A male subject, approximately 70 years of age; a dermoscopic close-up of a skin lesion.
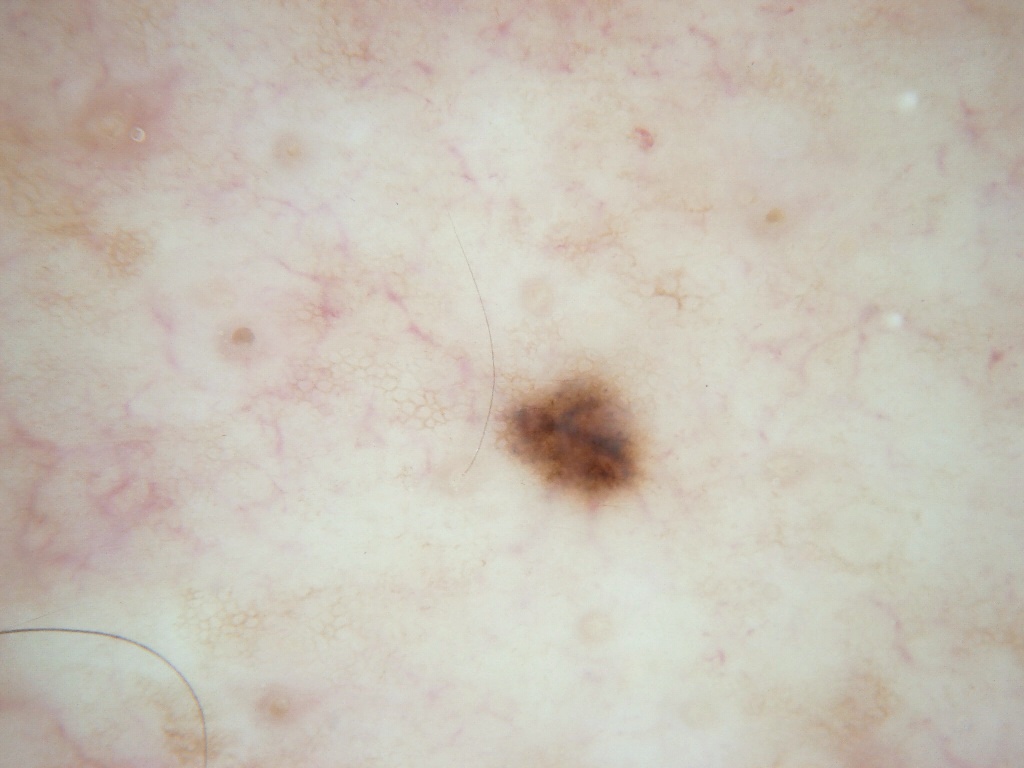Case summary:
– dermoscopic pattern — pigment network; absent: globules, streaks, negative network, and milia-like cysts
– size — small
– location — box(493, 363, 649, 512)
– diagnosis — a melanocytic nevus